A dermoscopic view of a skin lesion:
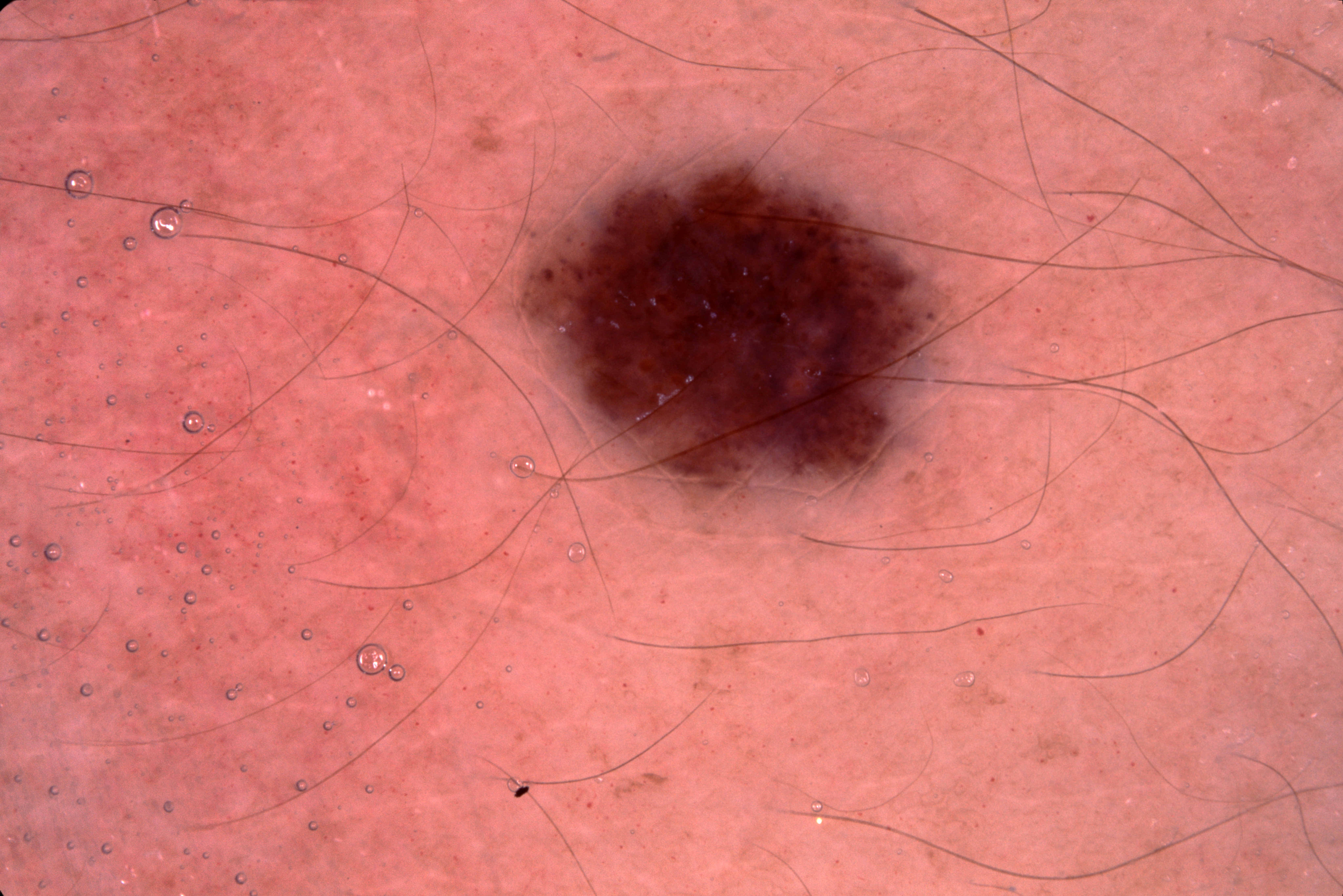dermoscopic features assessed but absent: negative network, pigment network, streaks, and milia-like cysts
lesion location: x1=520 y1=152 x2=959 y2=494
impression: a melanocytic nevus, a benign skin lesion